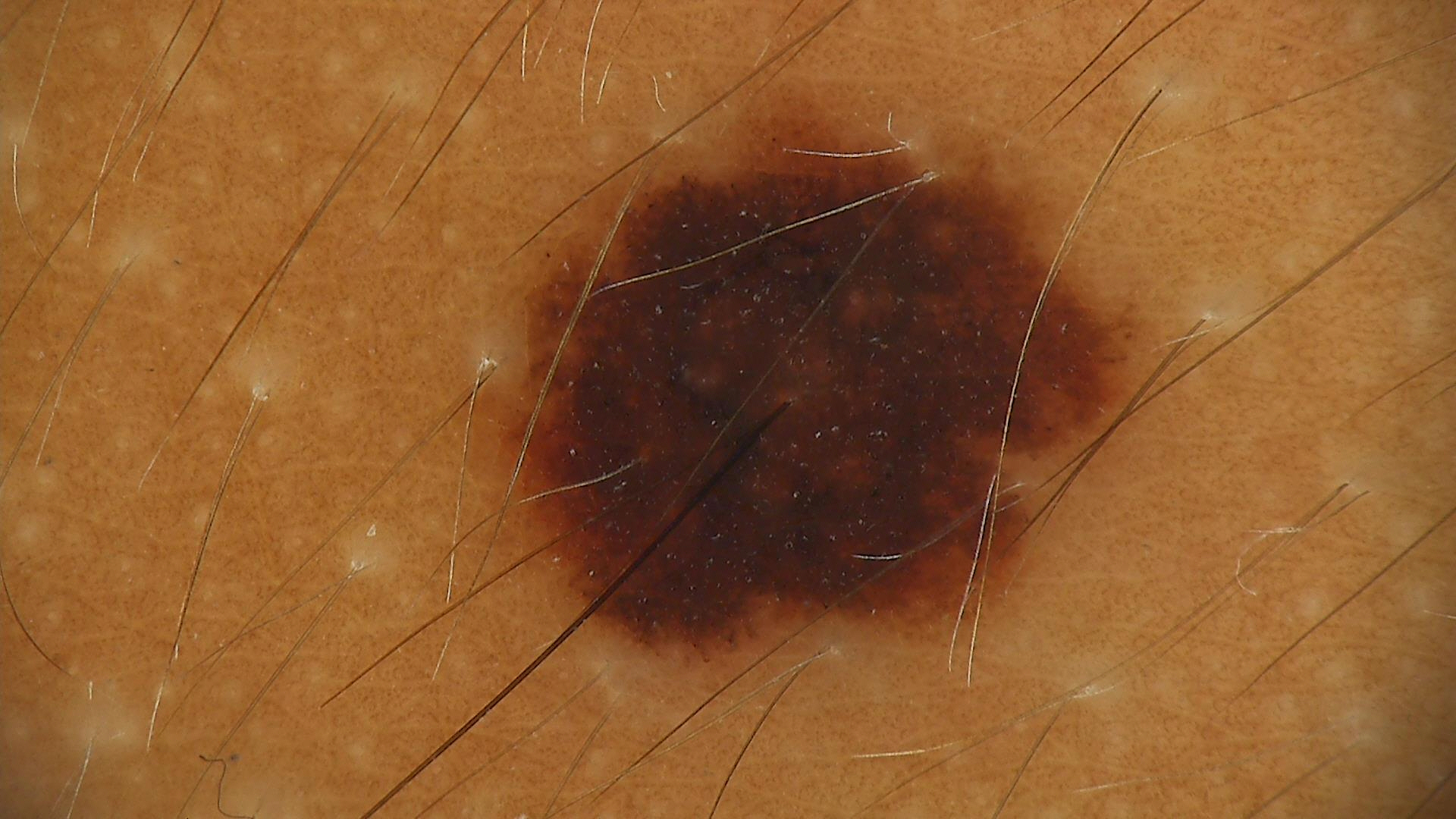image — dermatoscopy; class — dysplastic compound nevus (expert consensus).